A dermoscopic photograph of a skin lesion: 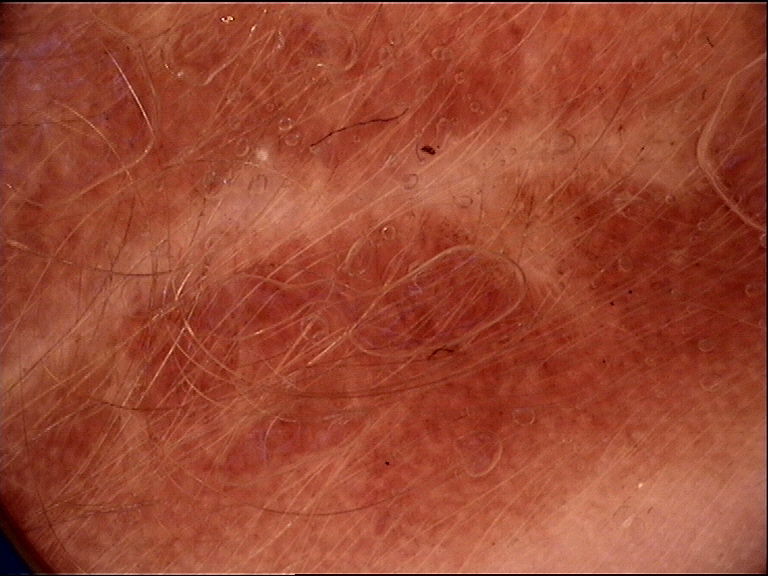Findings:
• subtype: banal
• diagnostic label: congenital junctional nevus (expert consensus)